A dermoscopic close-up of a skin lesion.
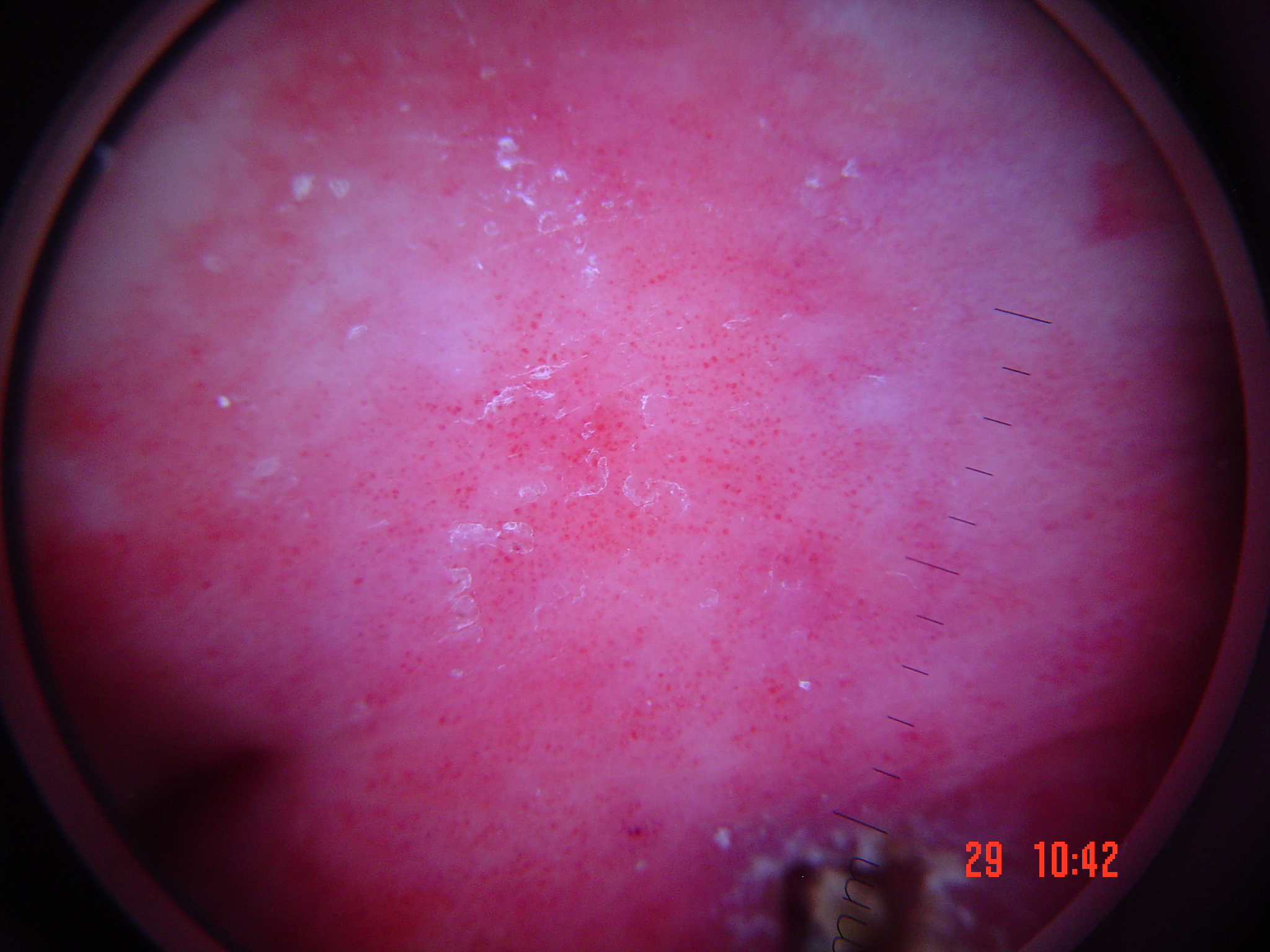The morphology is that of a vascular lesion. Consistent with a benign lesion — a hemangioma.